A skin lesion imaged with a dermatoscope:
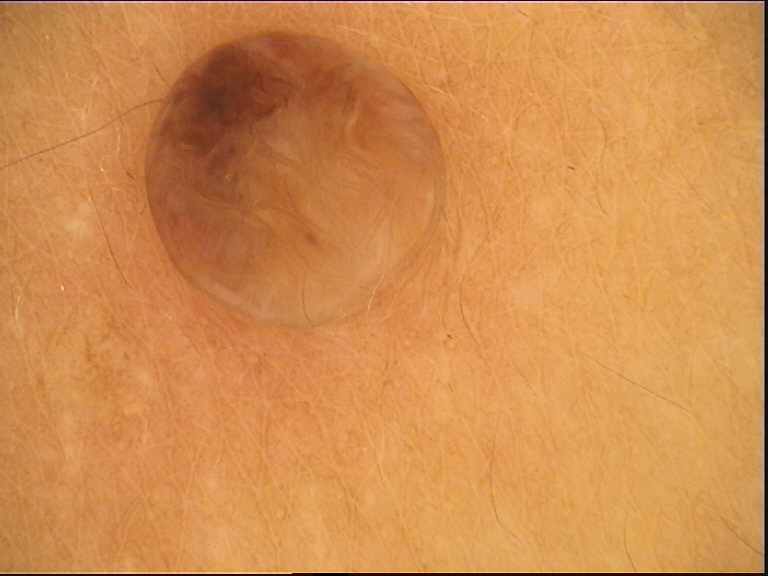subtype = banal; diagnostic label = dermal nevus (expert consensus).